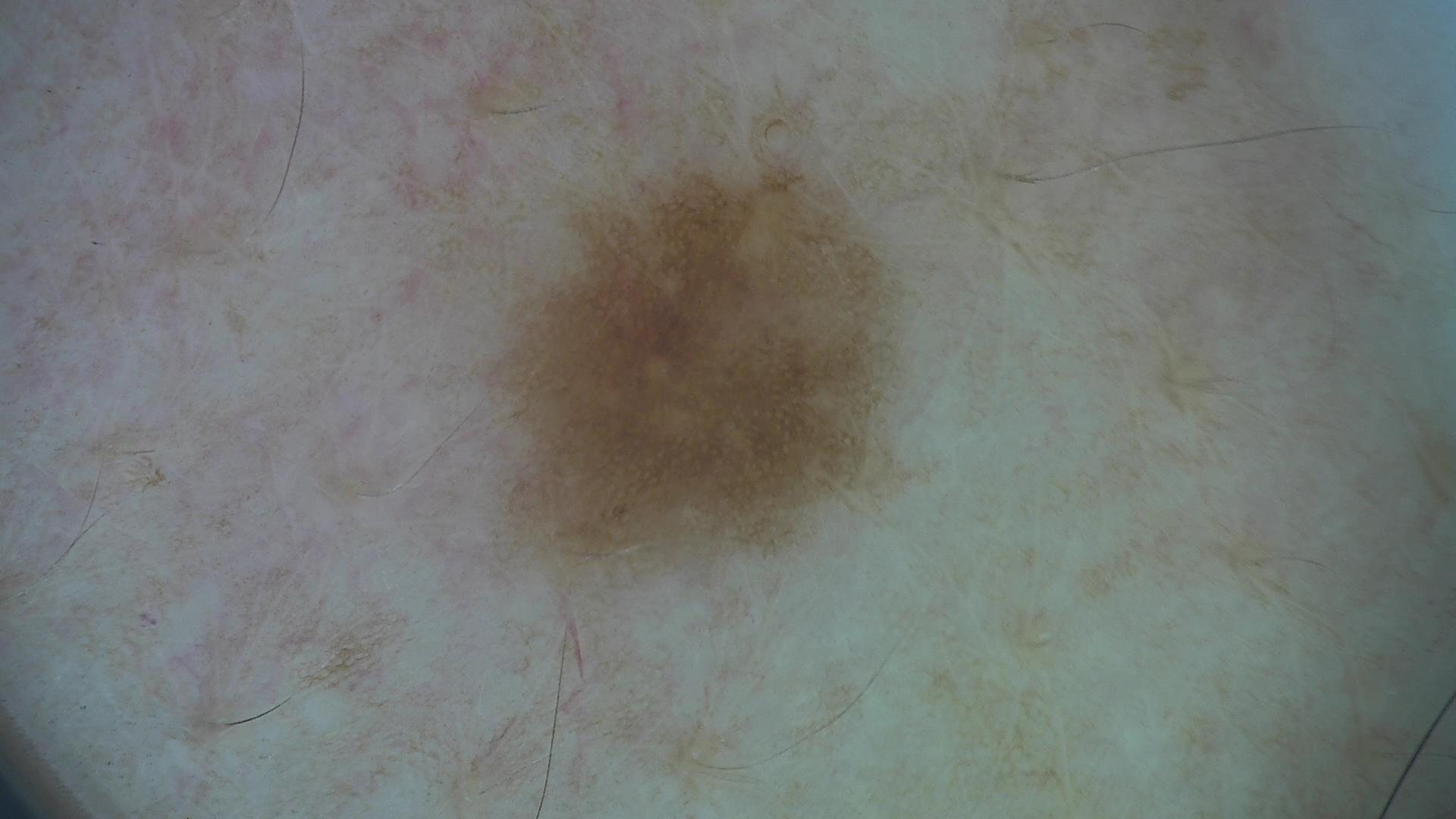Classified as a benign lesion — a dysplastic junctional nevus.